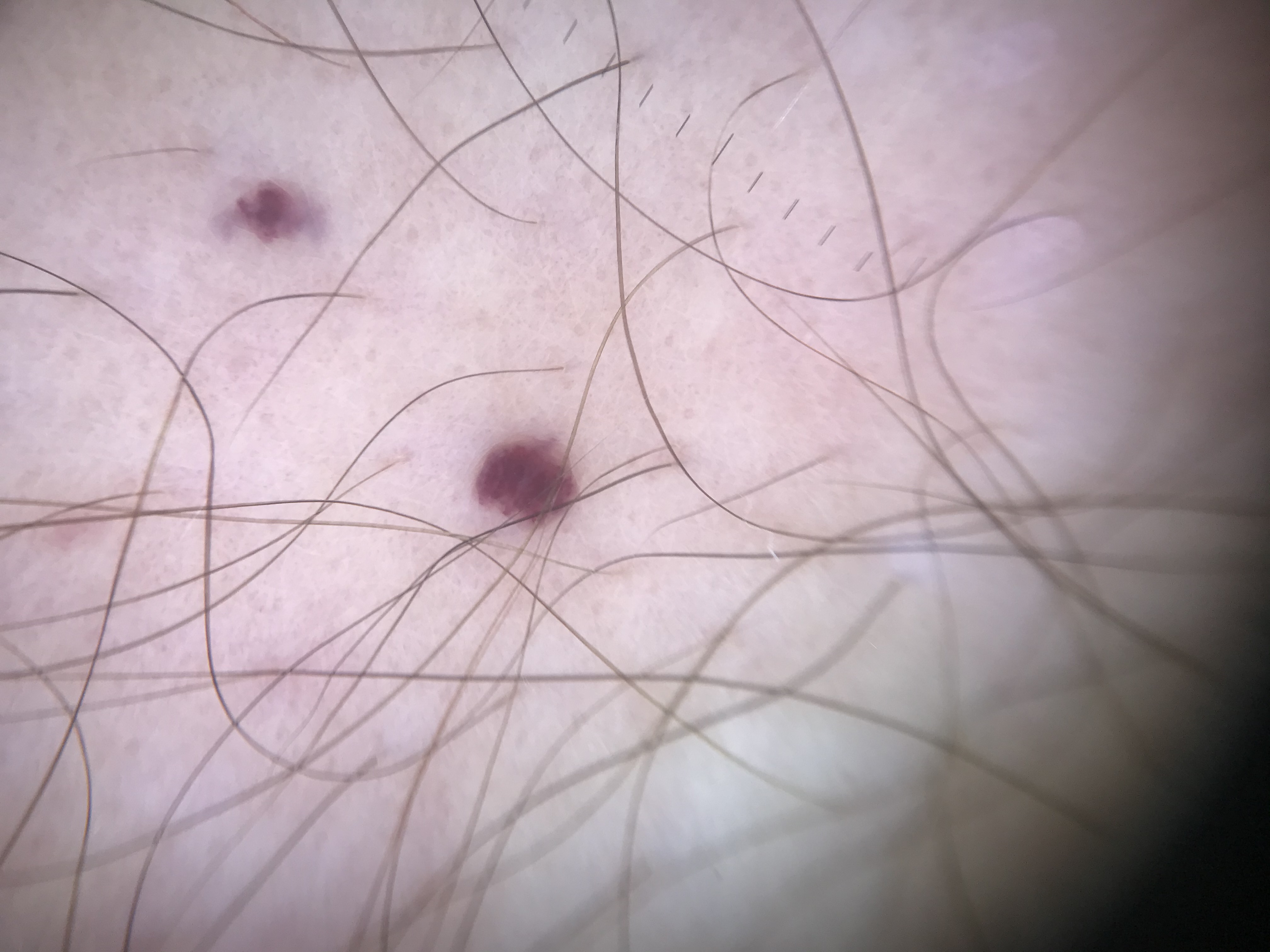Classified as a hemangioma.